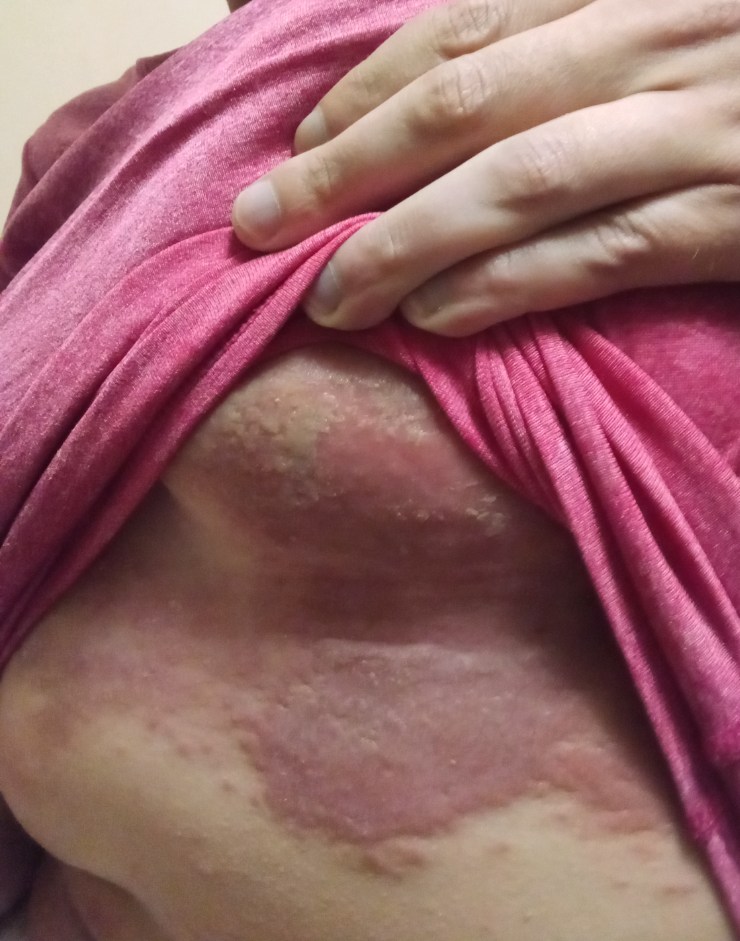Close-up view.
The patient reports associated chills.
The affected area is the front of the torso.
Present for less than one week.
Skin tone: lay reviewers estimated Monk Skin Tone 3.
The leading impression is Psoriasis; with consideration of Intertrigo; also raised was Candidal intertrigo.